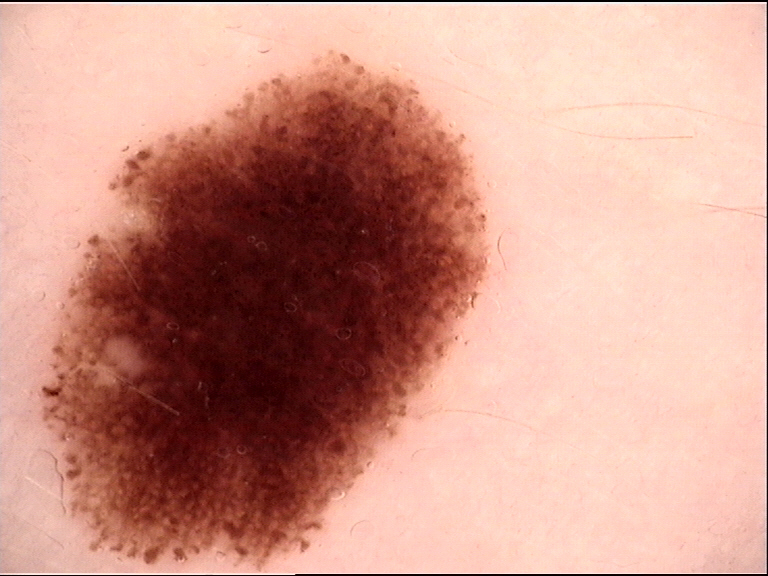Q: What kind of image is this?
A: dermoscopy
Q: What is this lesion?
A: dysplastic junctional nevus (expert consensus)